The patient described the issue as a rash. The lesion is described as raised or bumpy. The contributor reports enlargement, bothersome appearance and itching. An image taken at a distance. The head or neck and arm are involved: 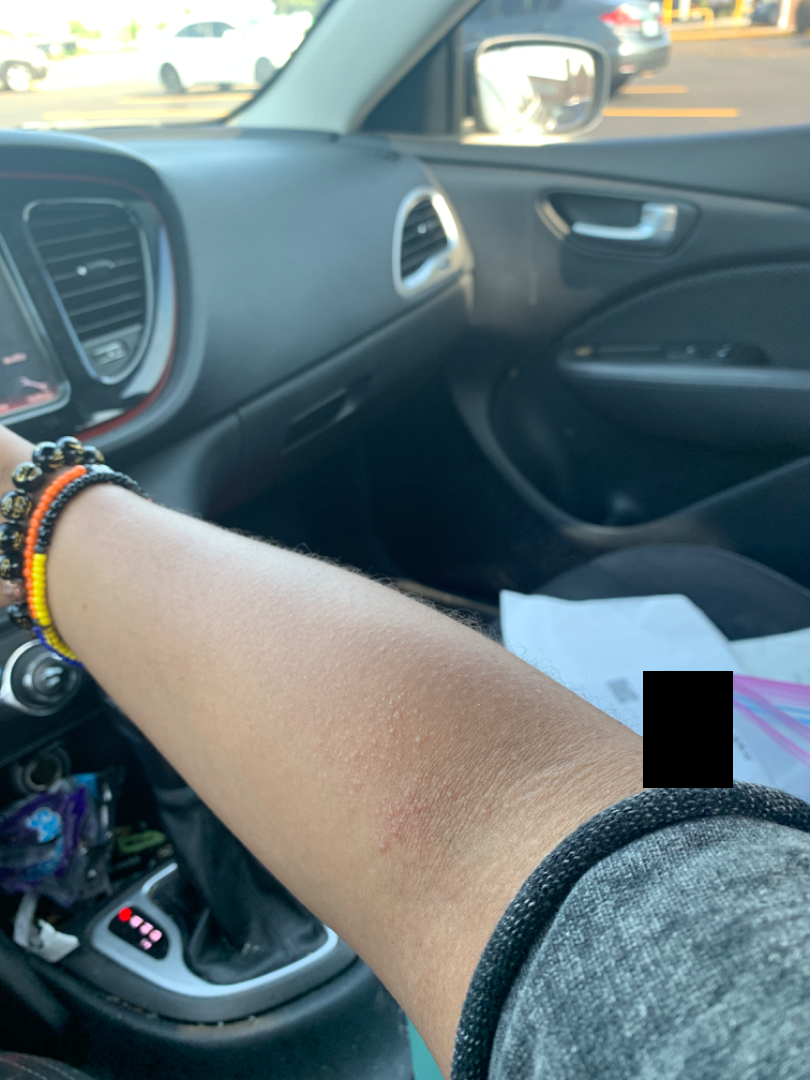Findings:
• impression — Lichen Simplex Chronicus (0.54); Acanthosis nigricans (0.23); PXE (pseudoxanthoma elasticum) like syndrome (0.23)